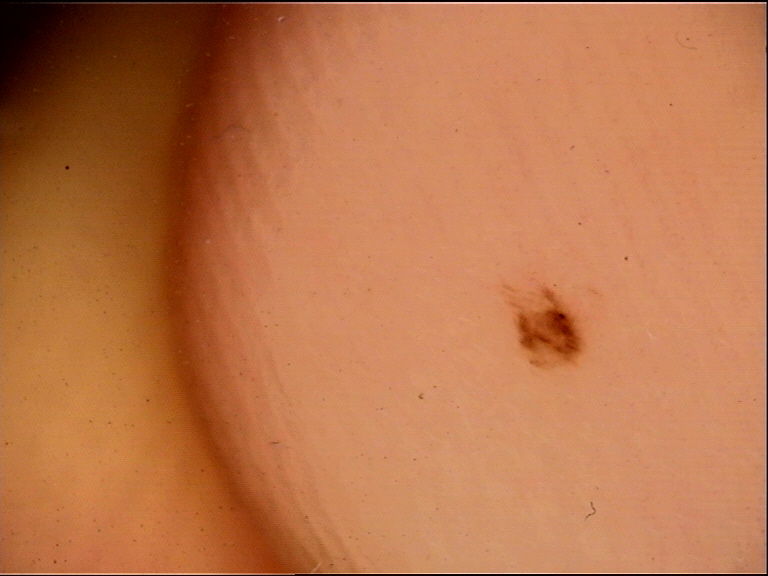image = dermatoscopy | class = acral dysplastic junctional nevus (expert consensus).